The patient is a male aged 13-17; a dermoscopy image of a single skin lesion: 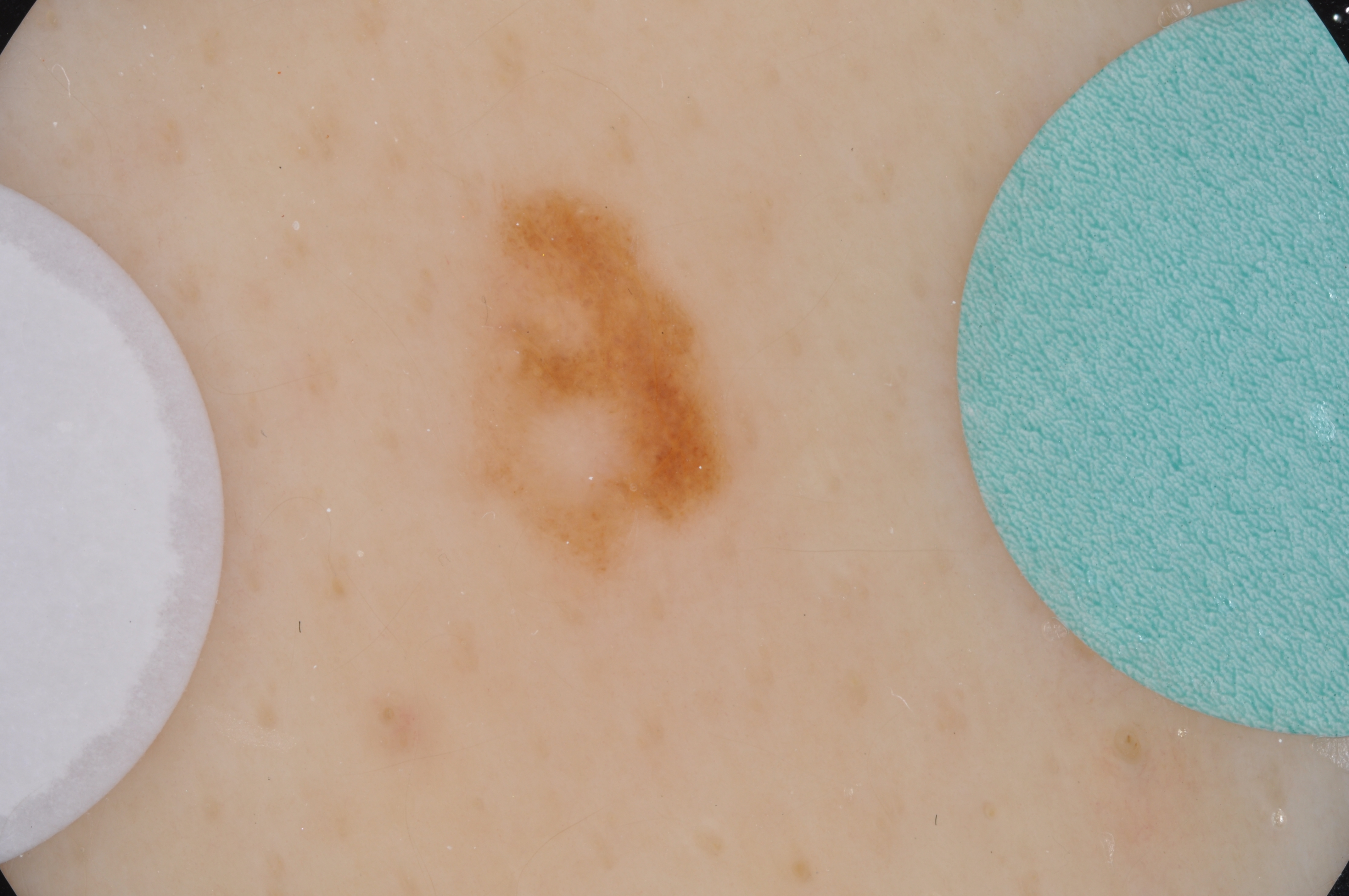* dermoscopic features not present: pigment network, milia-like cysts, streaks, globules, and negative network
* bounding box: [471,183,739,580]
* assessment: a melanocytic nevus, a benign skin lesion